Fitzpatrick phototype II · contact-polarized dermoscopy of a skin lesion · a female patient about 35 years old.
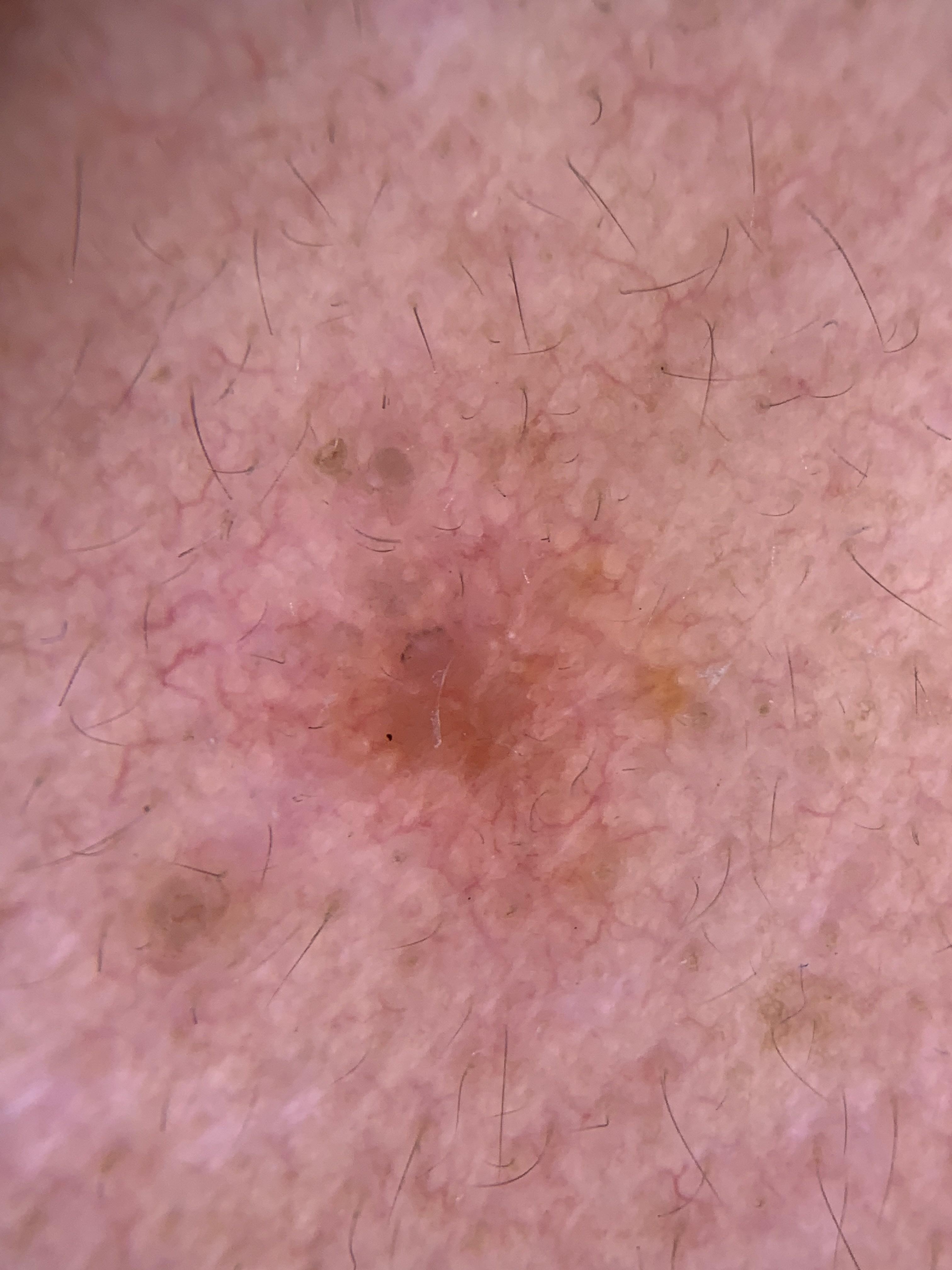The lesion was found on the head or neck. Confirmed on histopathology as a malignant lesion — a basal cell carcinoma.